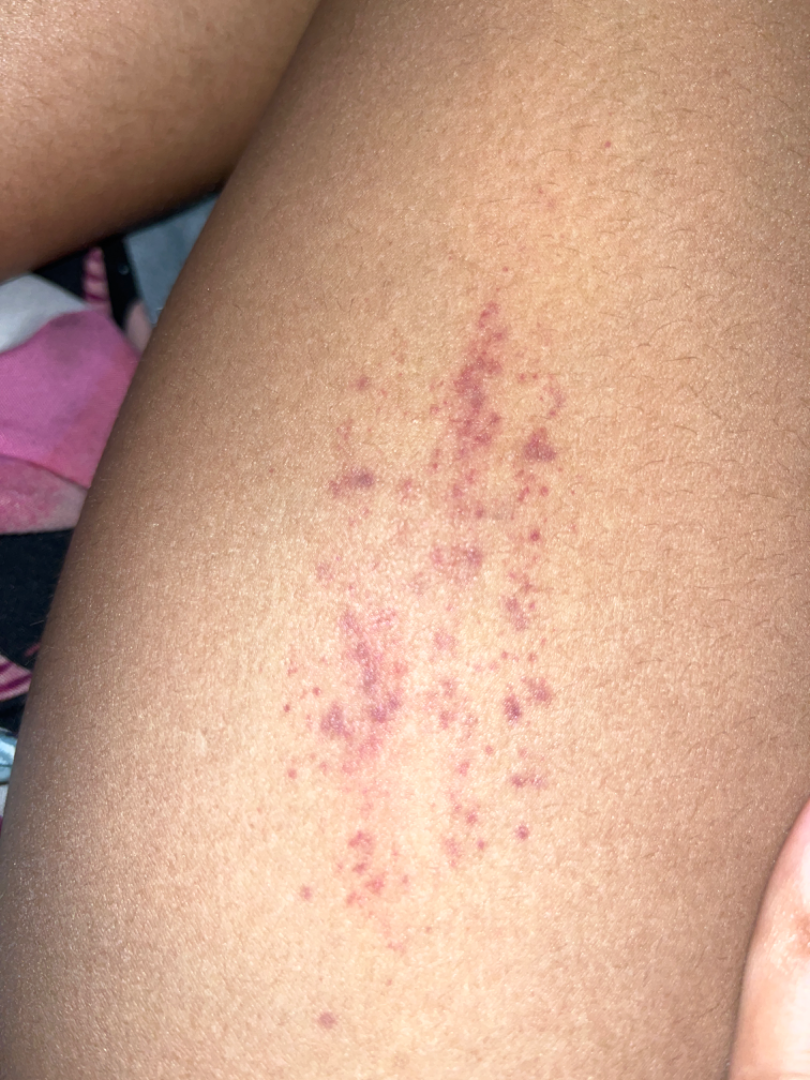| feature | finding |
|---|---|
| assessment | ungradable on photographic review |